Close-up view. The contributor is female. The lesion involves the sole of the foot and top or side of the foot.
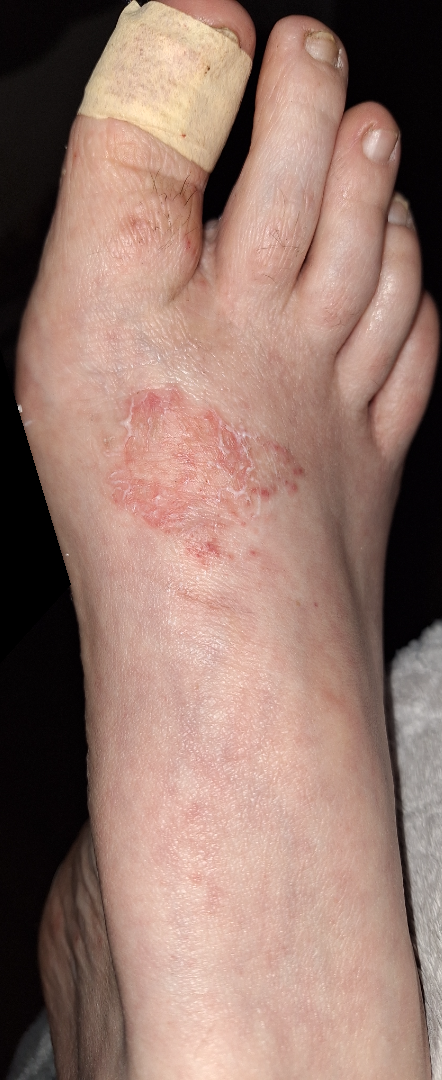Impression: The primary impression is Tinea; with consideration of Psoriasis; also raised was Eczema.